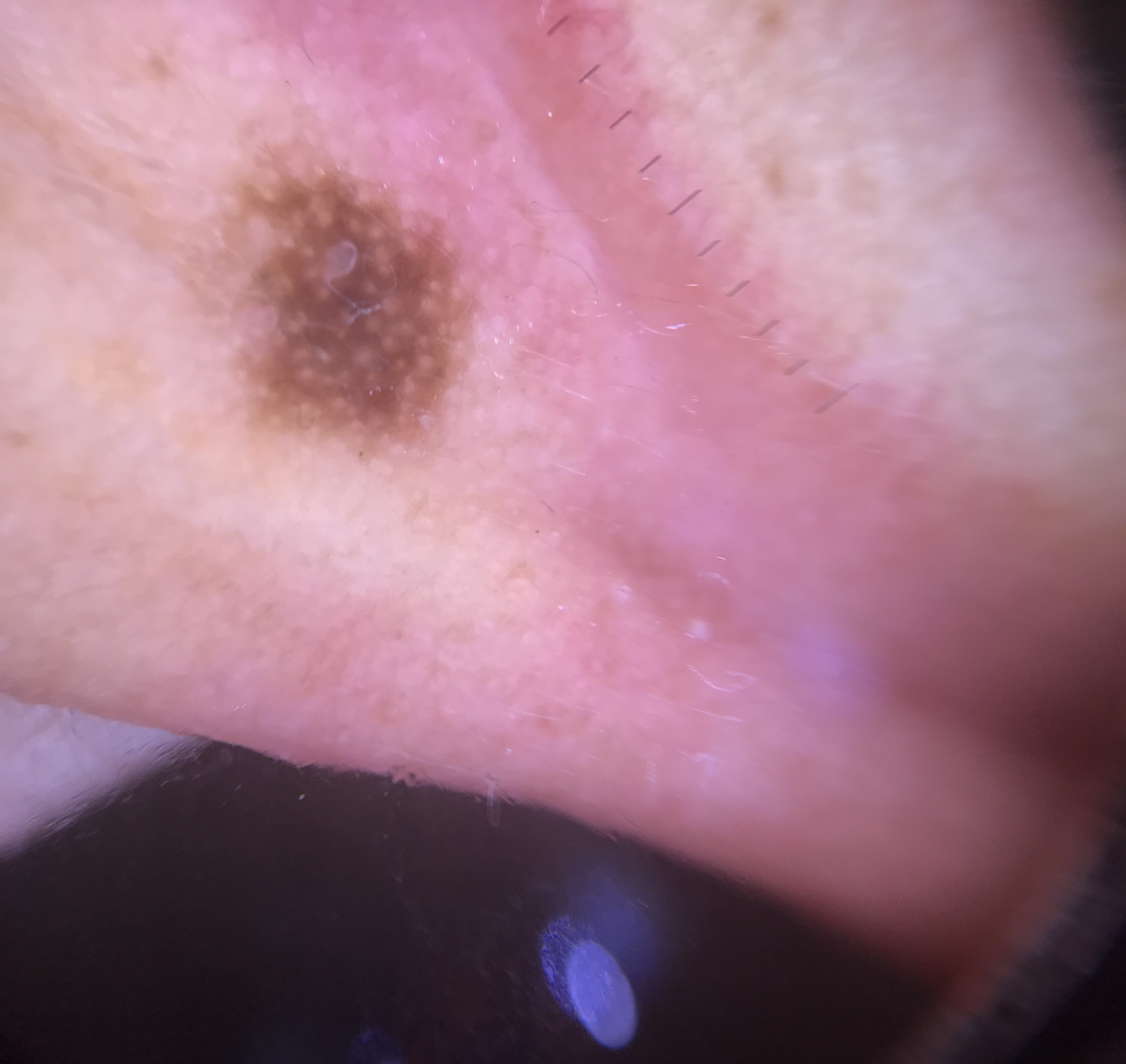{"image": "dermoscopy", "diagnosis": {"name": "acral dysplastic junctional nevus", "code": "ajd", "malignancy": "benign", "super_class": "melanocytic", "confirmation": "expert consensus"}}